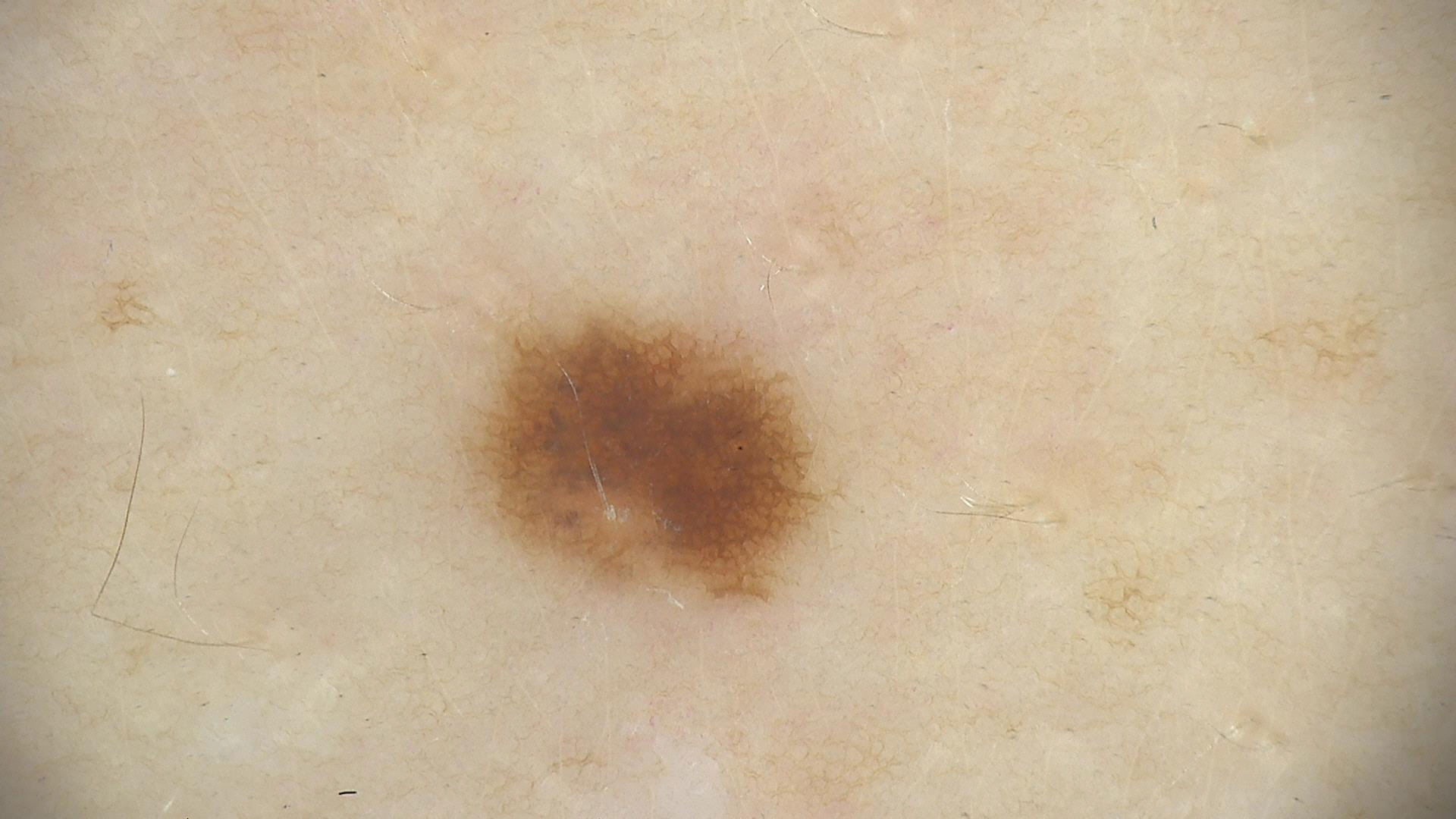<lesion>
  <diagnosis>
    <name>dysplastic junctional nevus</name>
    <code>jd</code>
    <malignancy>benign</malignancy>
    <super_class>melanocytic</super_class>
    <confirmation>expert consensus</confirmation>
  </diagnosis>
</lesion>